A dermatoscopic image of a skin lesion:
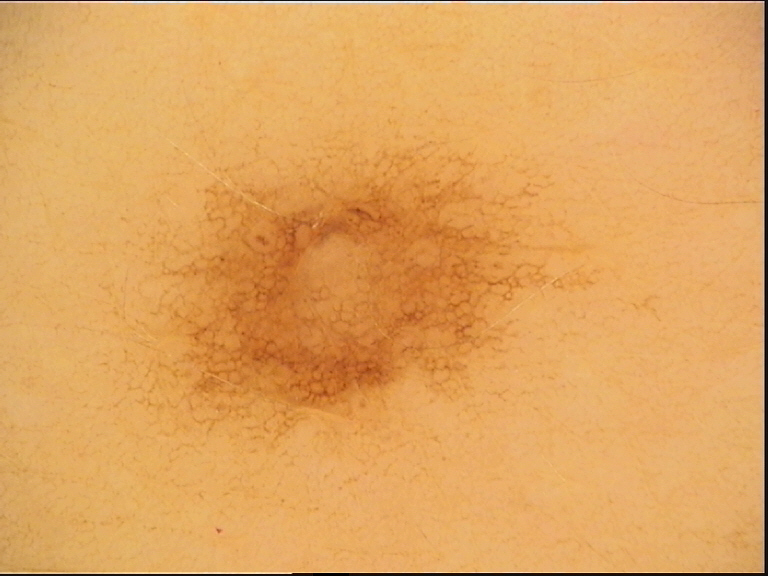Conclusion:
The diagnosis was a dysplastic junctional nevus.